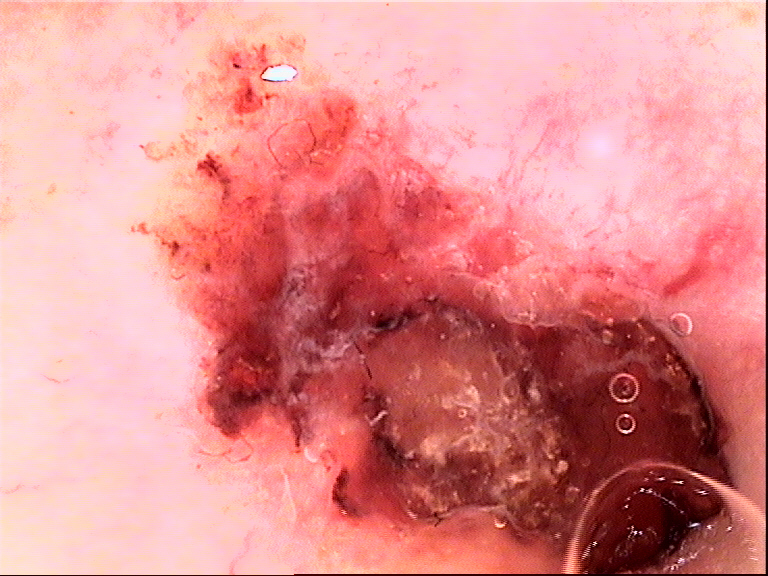Biopsy-confirmed as a malignant, keratinocytic lesion — a squamous cell carcinoma.